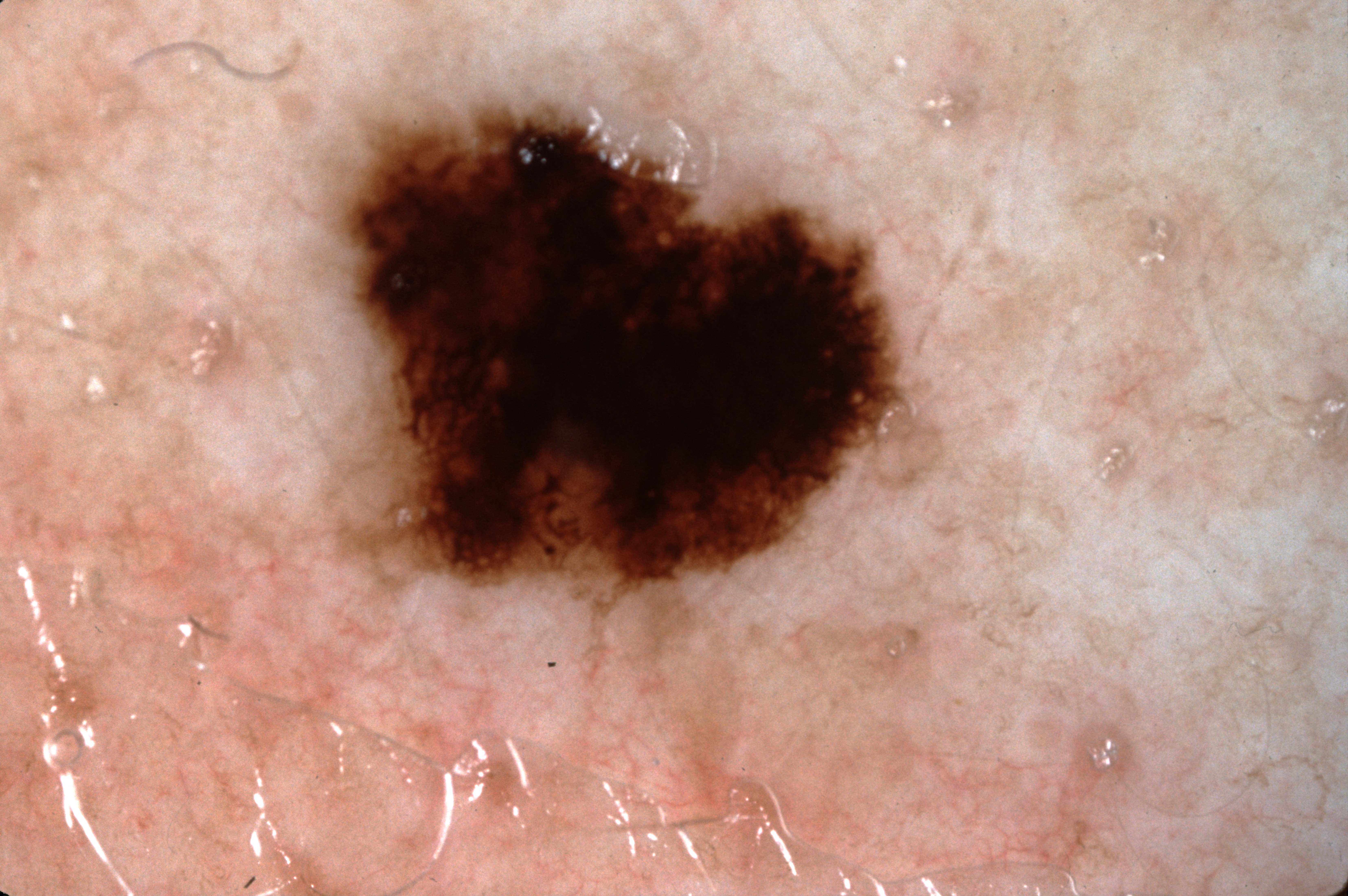Q: How was this image acquired?
A: dermoscopic image
Q: Where is the lesion located?
A: x1=337, y1=105, x2=906, y2=602
Q: What is the diagnosis?
A: a melanoma, a malignant lesion